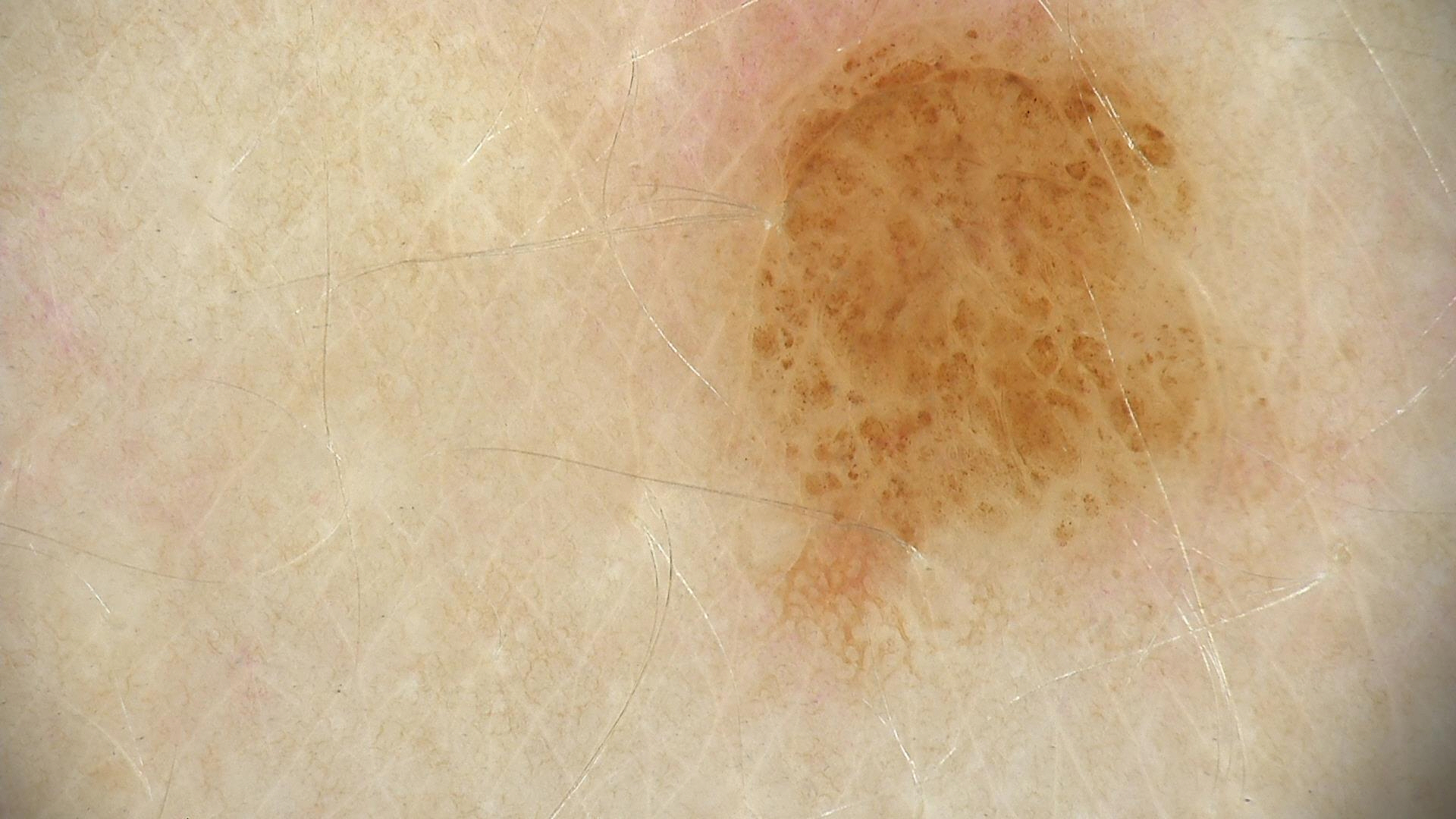Dermoscopy of a skin lesion.
Consistent with a banal lesion — a compound nevus.